A skin lesion imaged with a dermatoscope; a female subject 60 years old; few moles overall by the patient's own estimate; referred with a clinical suspicion of basal cell carcinoma: 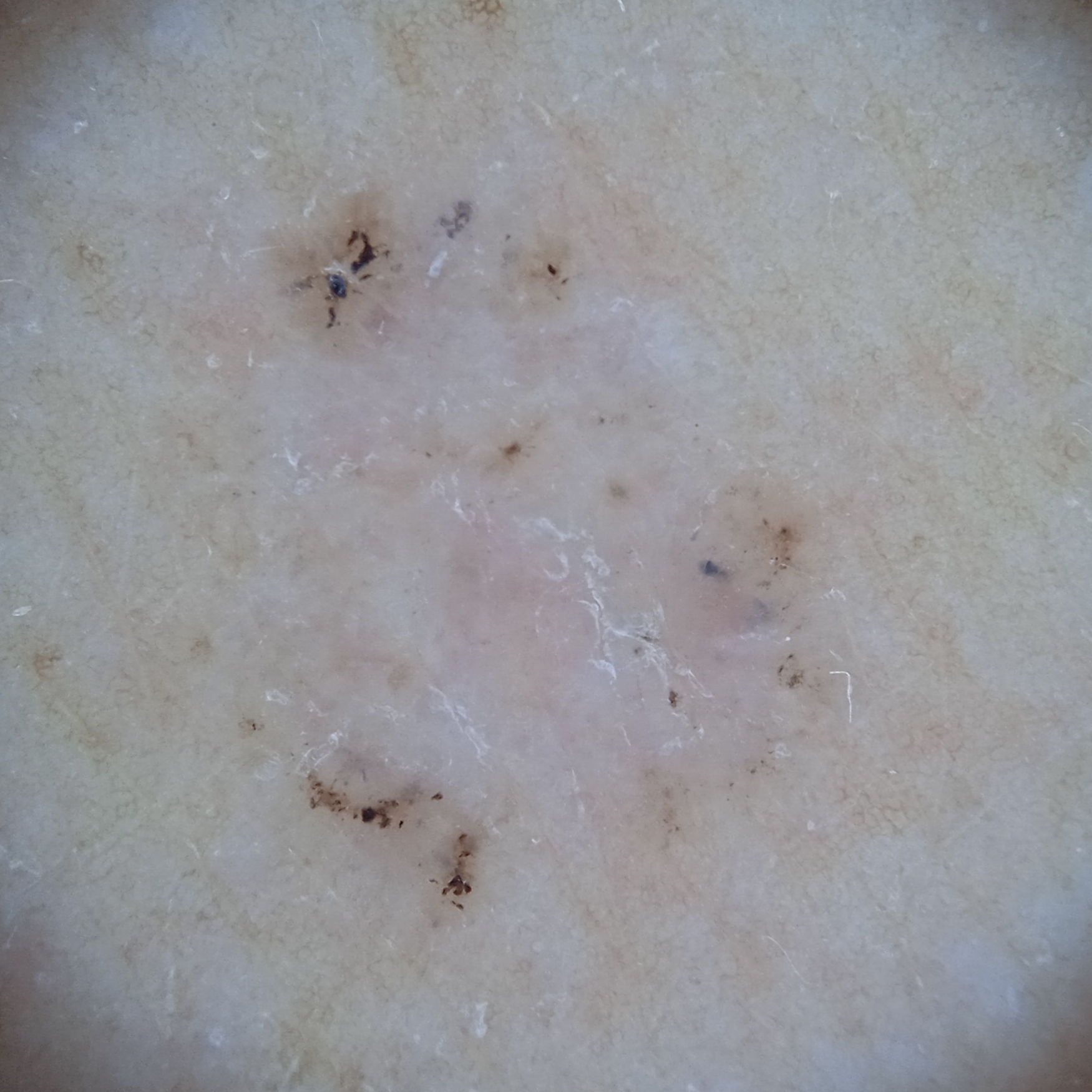location: the back; diagnostic label: basal cell carcinoma (dermatologist consensus).